This image was taken at an angle — 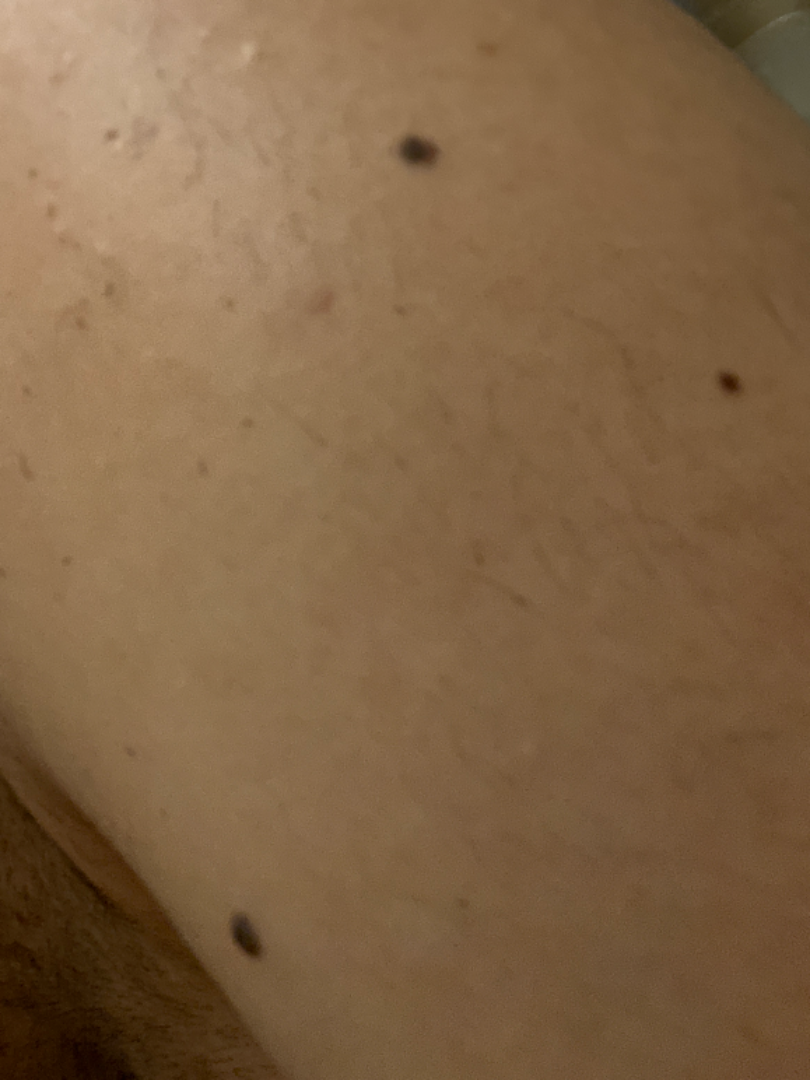Notes:
- assessment — not assessable